A female subject 58 years old · a clinical close-up photograph of a skin lesion: 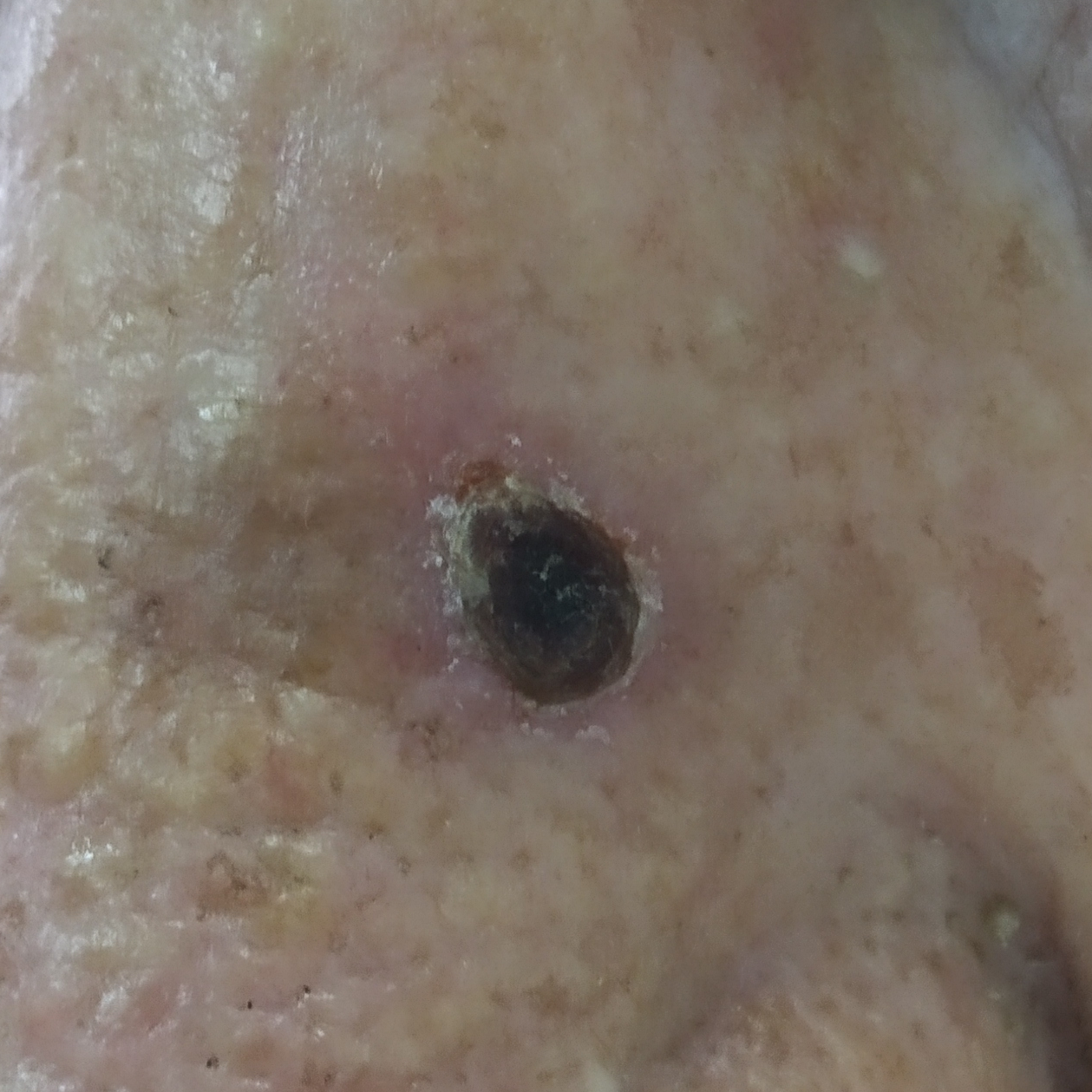The patient describes that the lesion has grown, has bled, and is elevated.
Histopathological examination showed a basal cell carcinoma.